The patient is a male about 45 years old. Dermoscopy of a skin lesion: 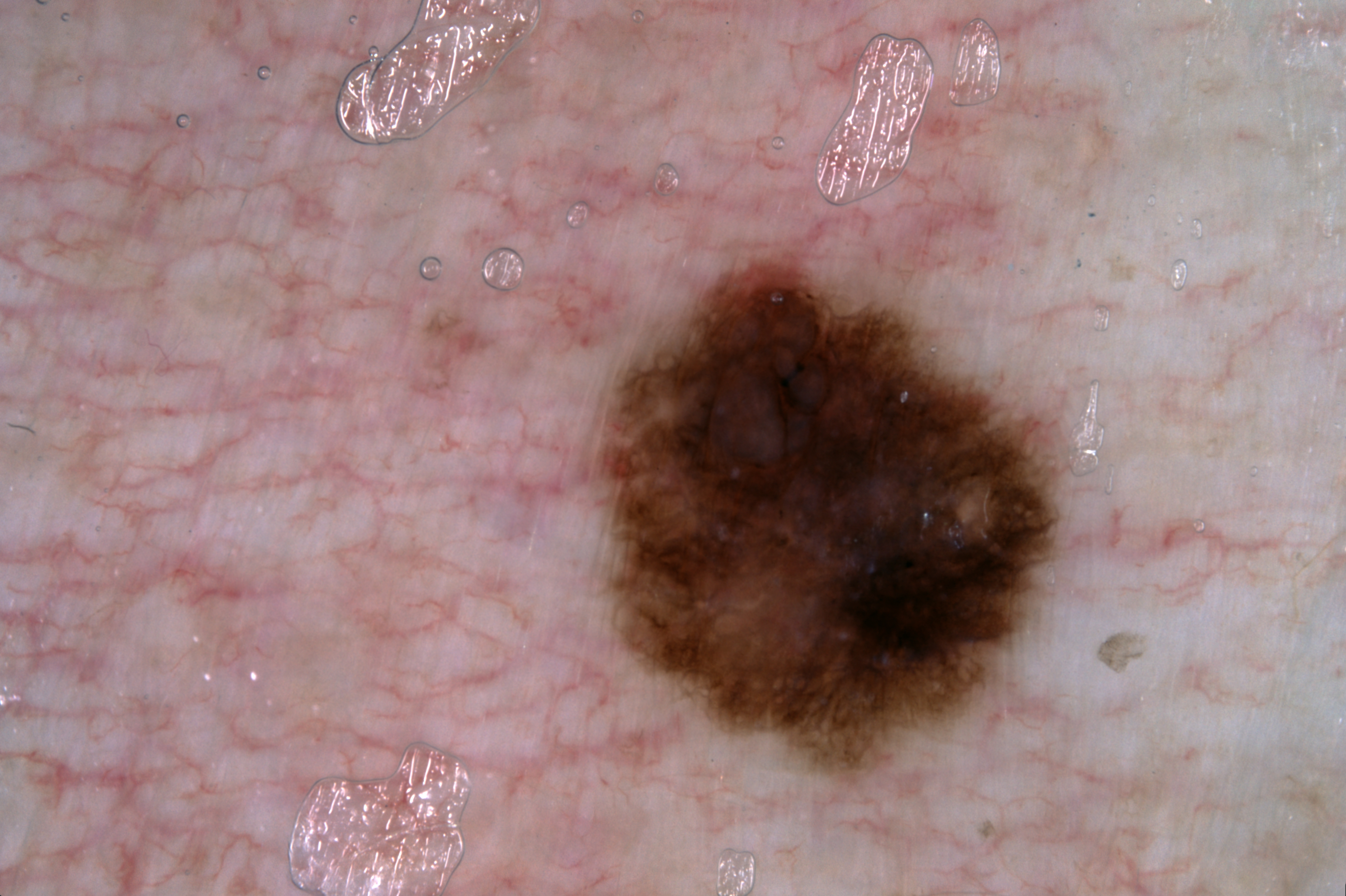The lesion takes up a moderate portion of the field. Dermoscopic review identifies pigment network, with no negative network, milia-like cysts, or streaks. With coordinates (x1, y1, x2, y2), lesion location: 600/259/1062/770. The clinical diagnosis was a melanocytic nevus, a benign skin lesion.